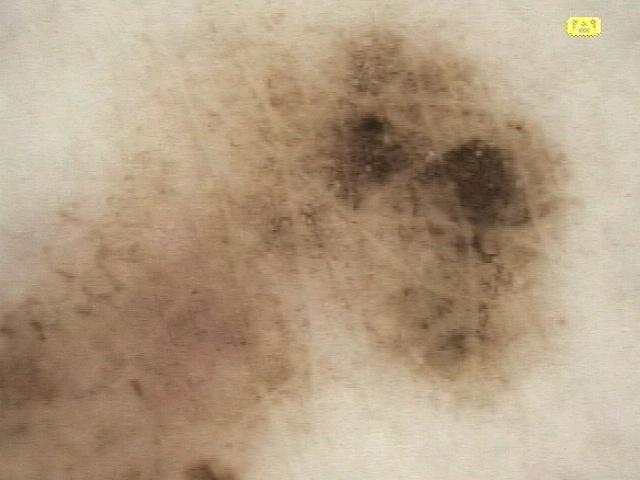Histopathology confirmed a melanoma.